Associated systemic symptoms include fever, fatigue, joint pain and shortness of breath · self-categorized by the patient as a rash · the patient reports itching · texture is reported as raised or bumpy · reported duration is more than one year · the arm, leg and head or neck are involved · female subject, age 50–59 · a close-up photograph.
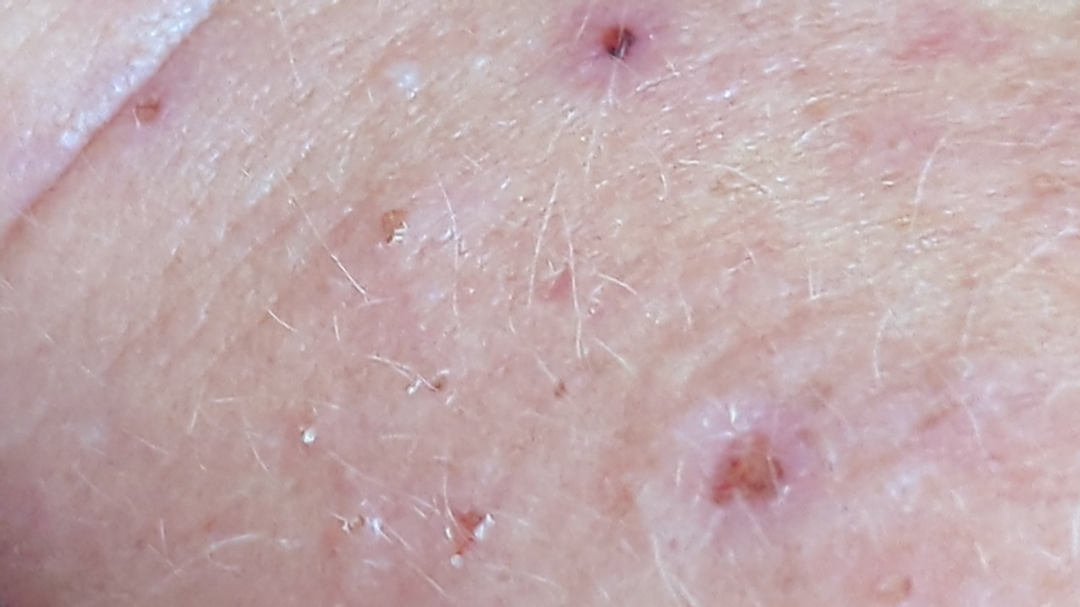On photographic review: the leading consideration is Prurigo nodularis; an alternative is Inflicted skin lesions; also raised was Actinic Keratosis; less likely is Skin infection.